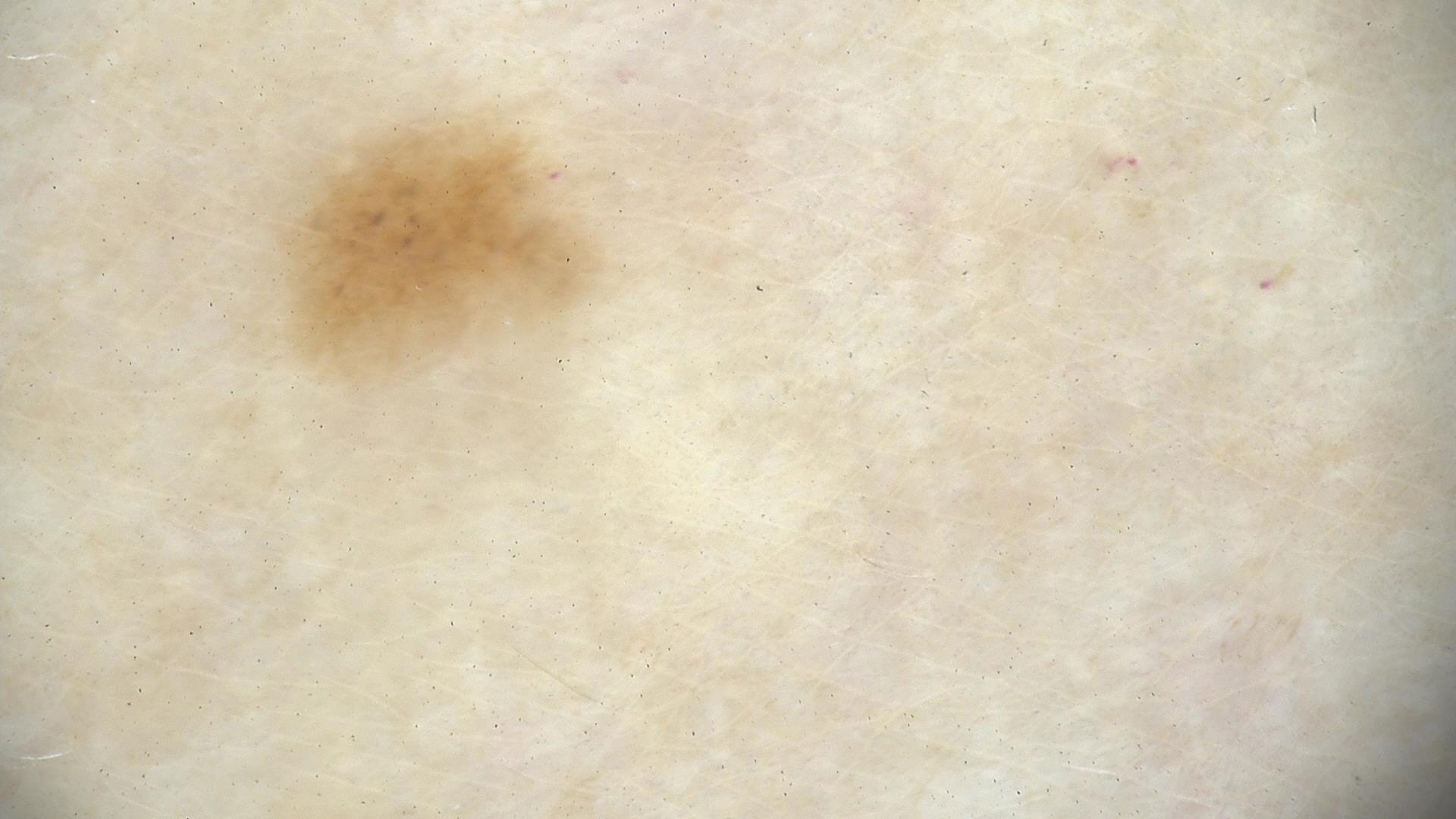– class · dysplastic junctional nevus (expert consensus)